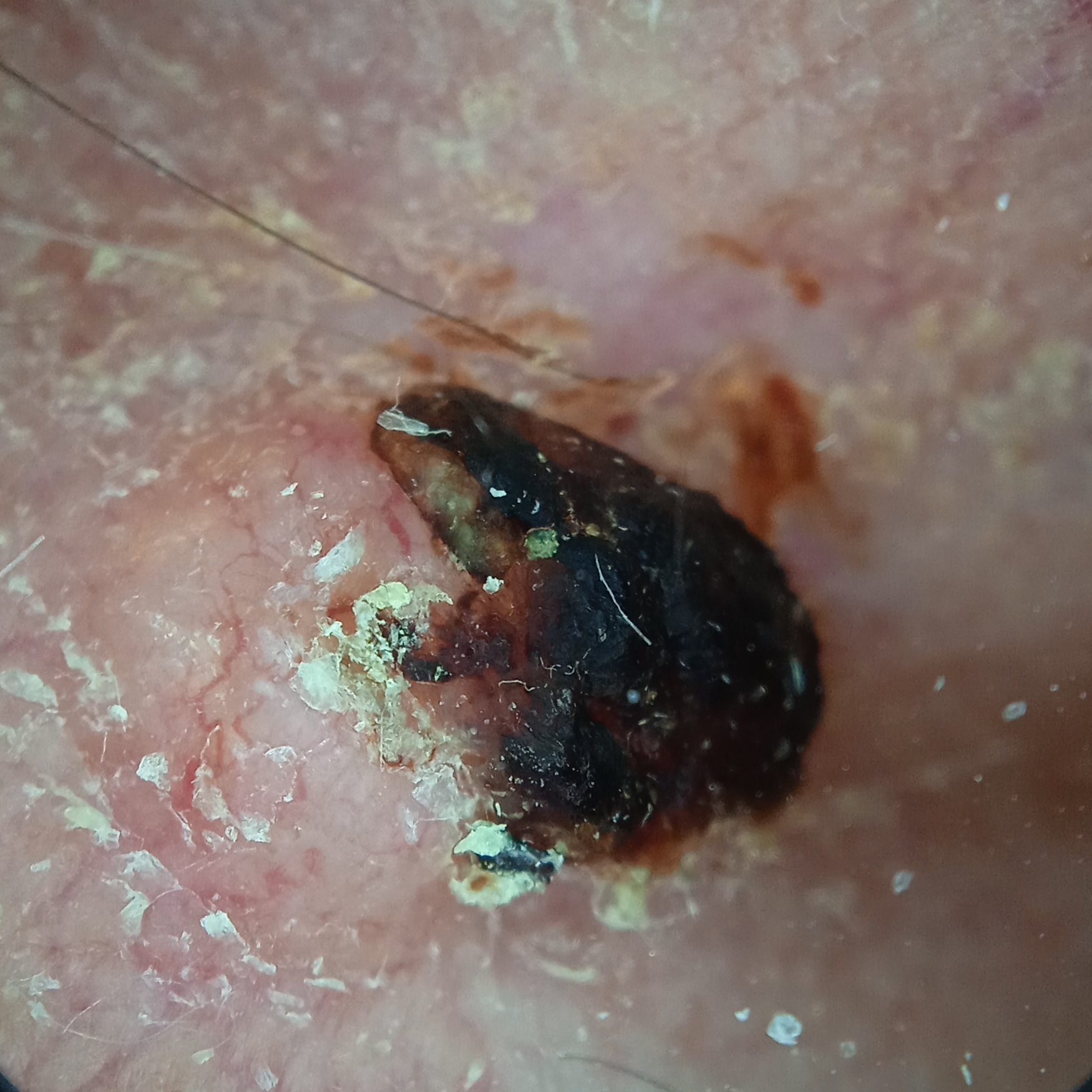Findings:
– image type — dermatoscopic image
– referral context — clinical suspicion of basal cell carcinoma
– anatomic site — the head
– diagnosis — basal cell carcinoma (biopsy-proven)